Located on the arm, this is a close-up image: 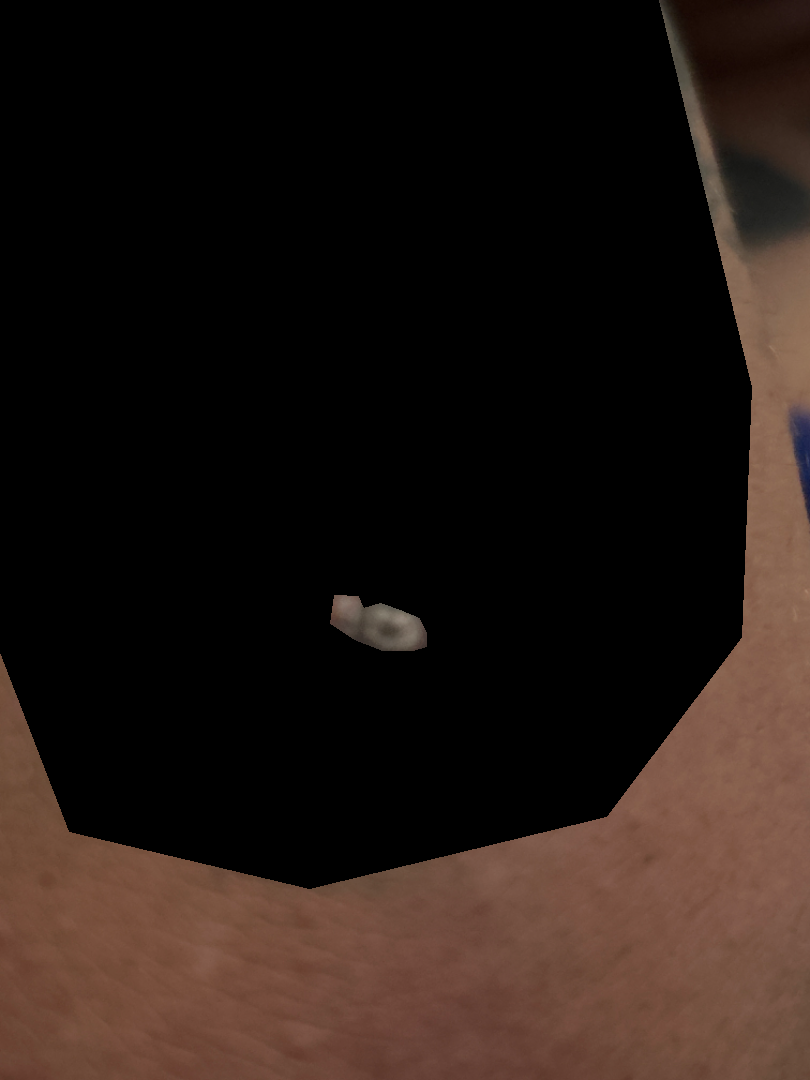Findings:
The condition could not be reliably identified from the image.